Dermoscopy of a skin lesion; a male patient, roughly 65 years of age:
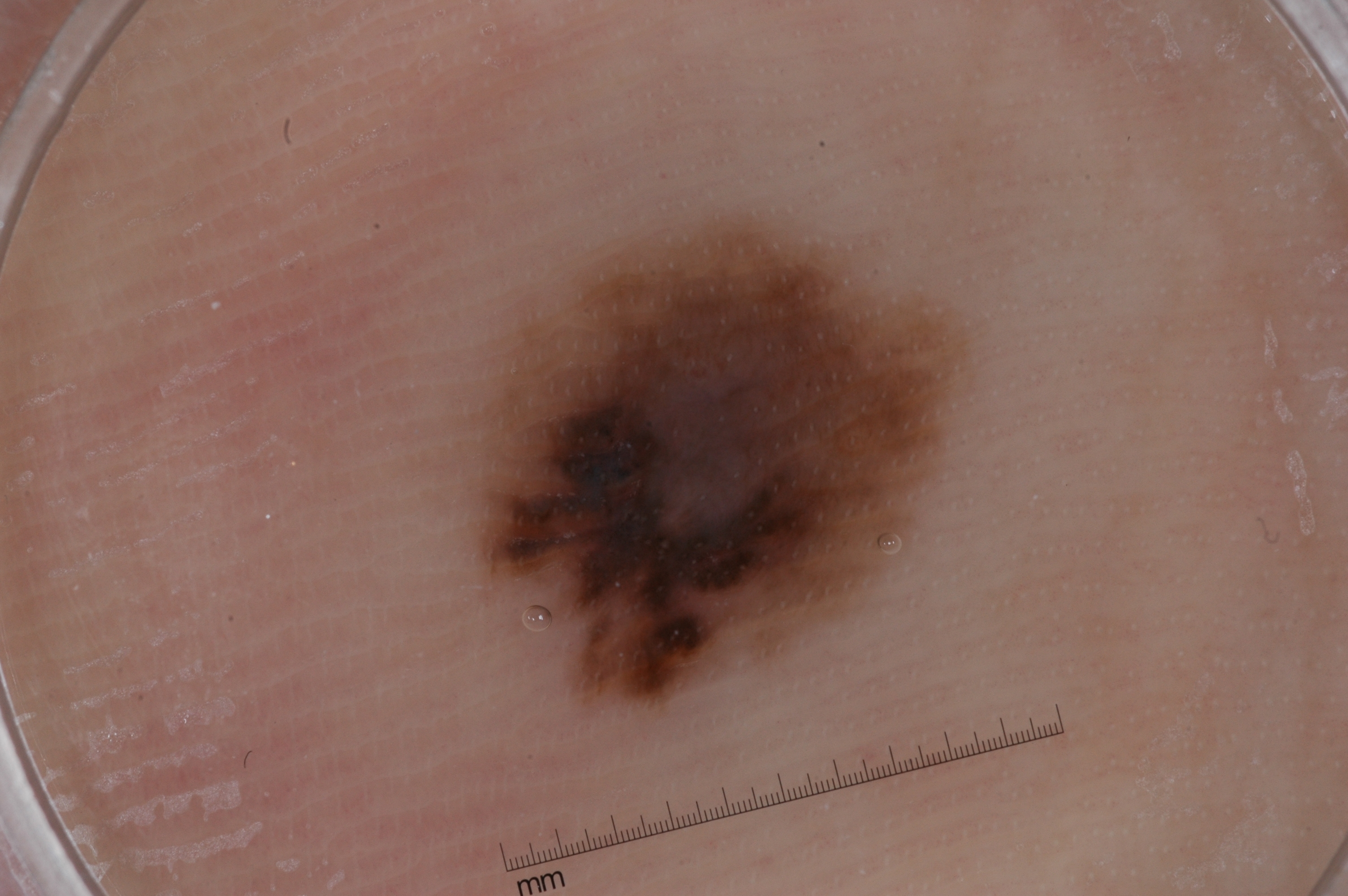With coordinates (x1, y1, x2, y2), lesion location: [485,224,958,700]. On dermoscopy, the lesion shows no streaks, pigment network, negative network, or milia-like cysts. Expert review diagnosed this as a melanocytic nevus, a benign lesion.